A skin lesion imaged with a dermatoscope: 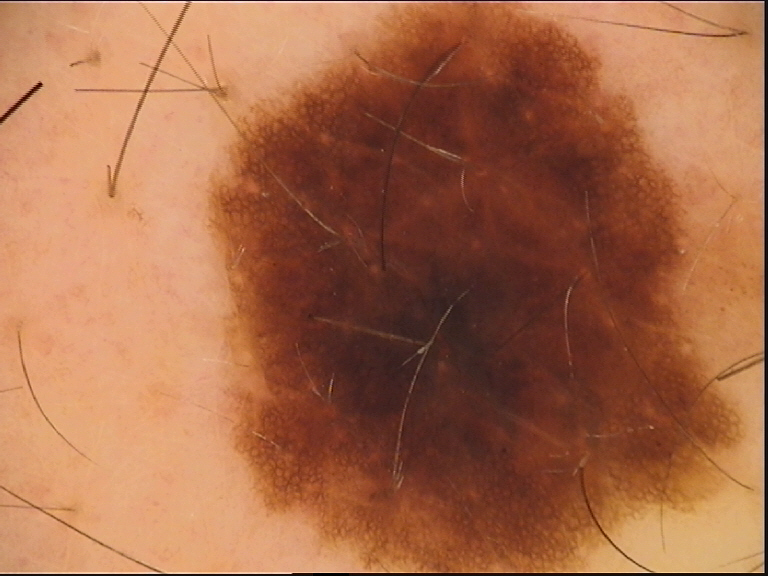label=dysplastic compound nevus (expert consensus).